A dermoscopy image of a single skin lesion.
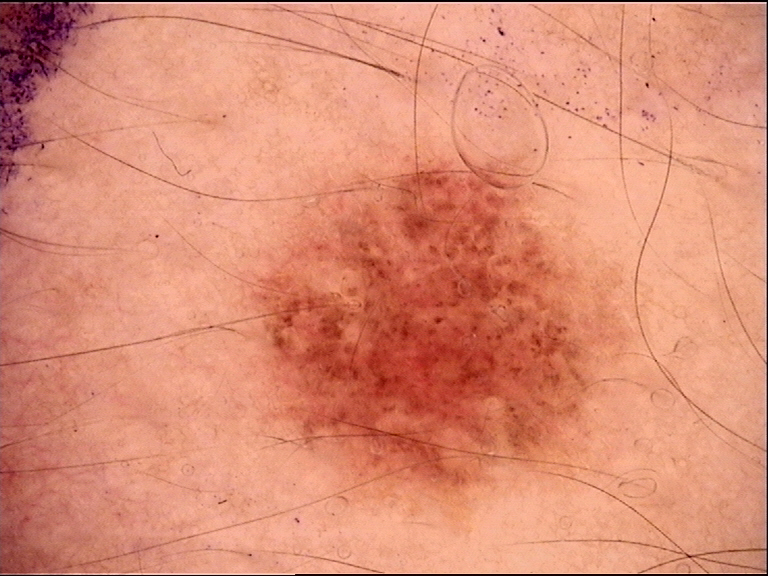Q: What is the diagnosis?
A: dysplastic junctional nevus (expert consensus)